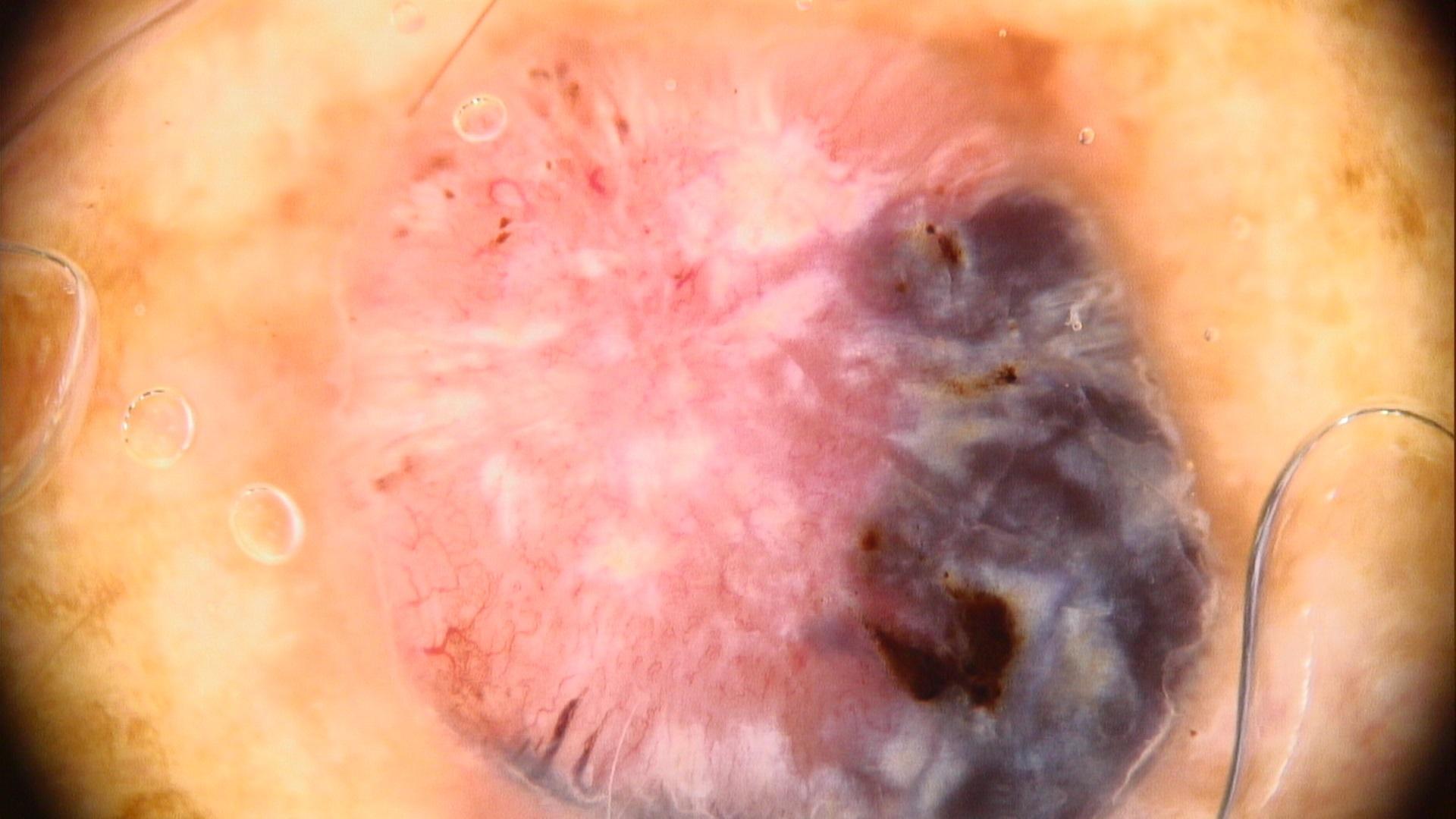Findings:
• patient — male, in their mid- to late 70s
• modality — contact-polarized dermoscopy
• skin phototype — III
• location — the trunk
• pathology — Melanoma (biopsy-proven)